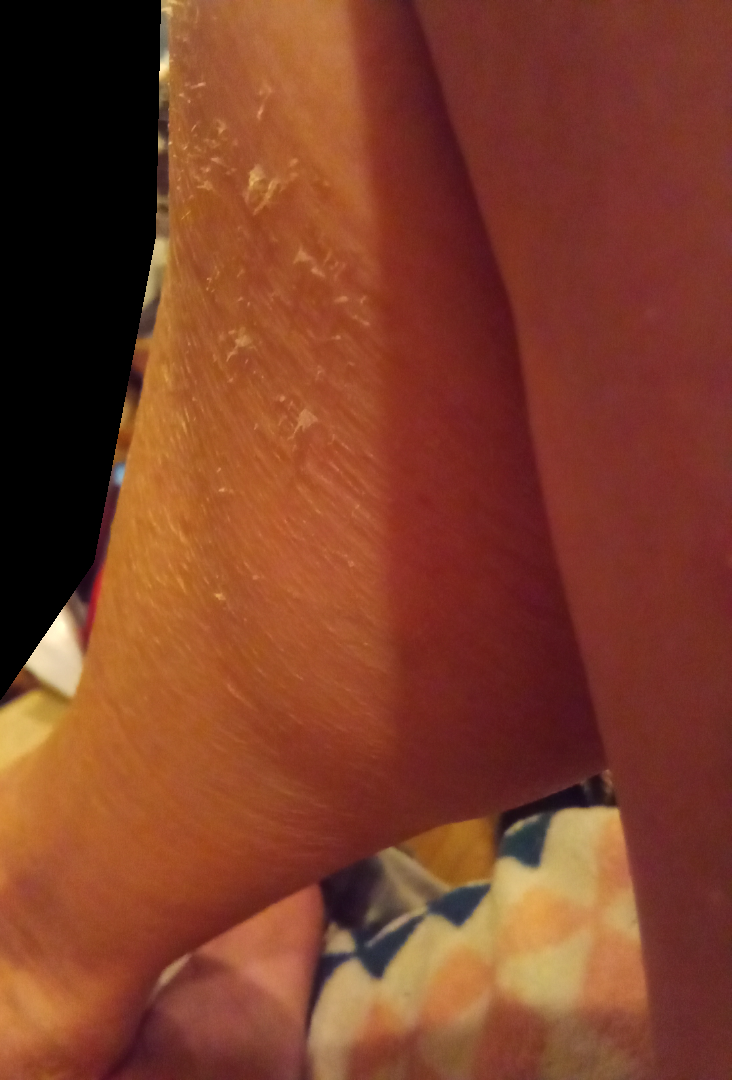On photographic review, the impression was split between Xerosis, Ichthyosis and Eczema.